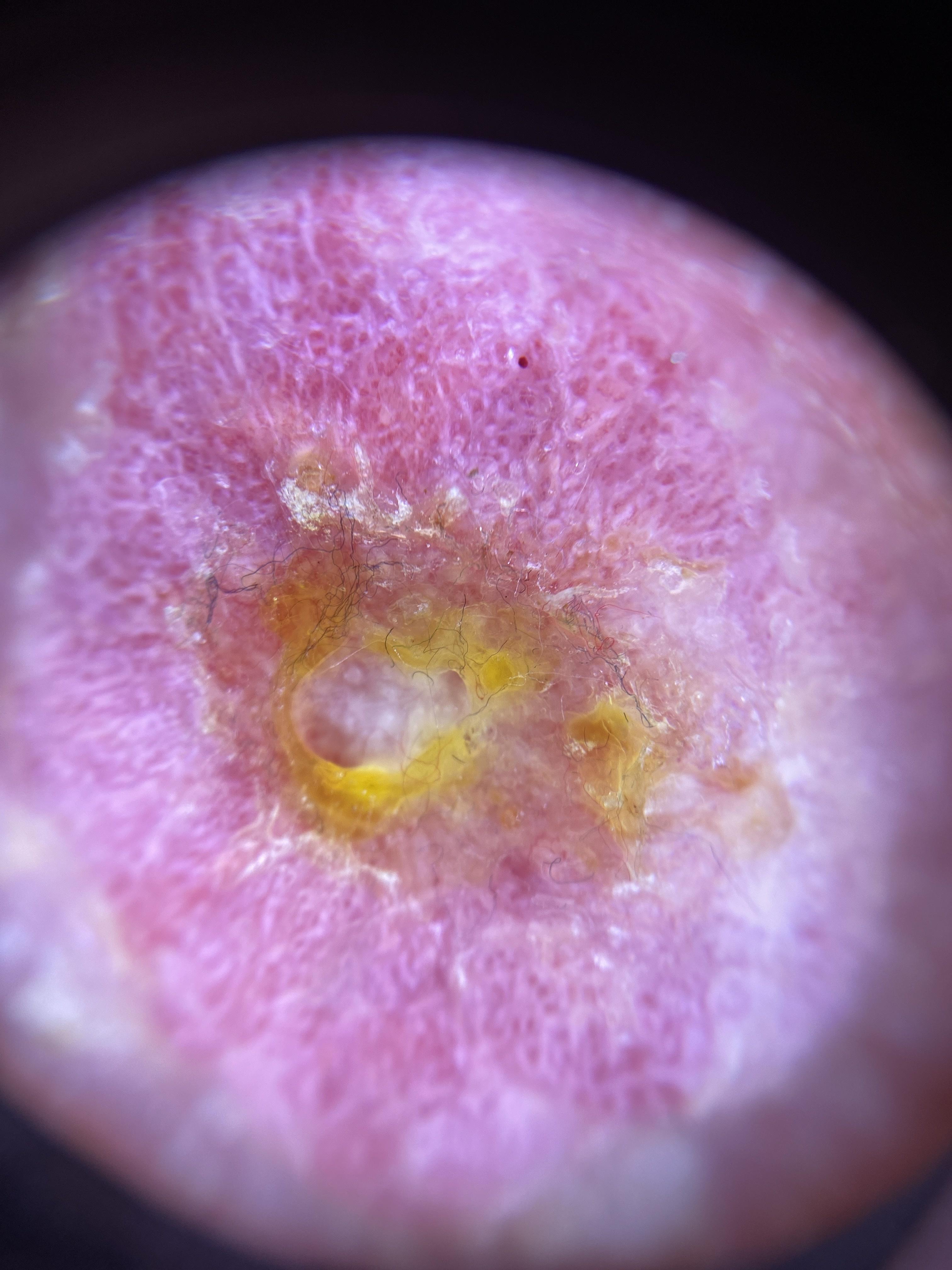Findings:
A dermoscopy image of a single skin lesion. Per the chart, a previous melanoma. A male patient approximately 85 years of age or older. The lesion is located on a lower extremity.
Conclusion:
The biopsy diagnosis was a malignant, epidermal lesion — a squamous cell carcinoma.